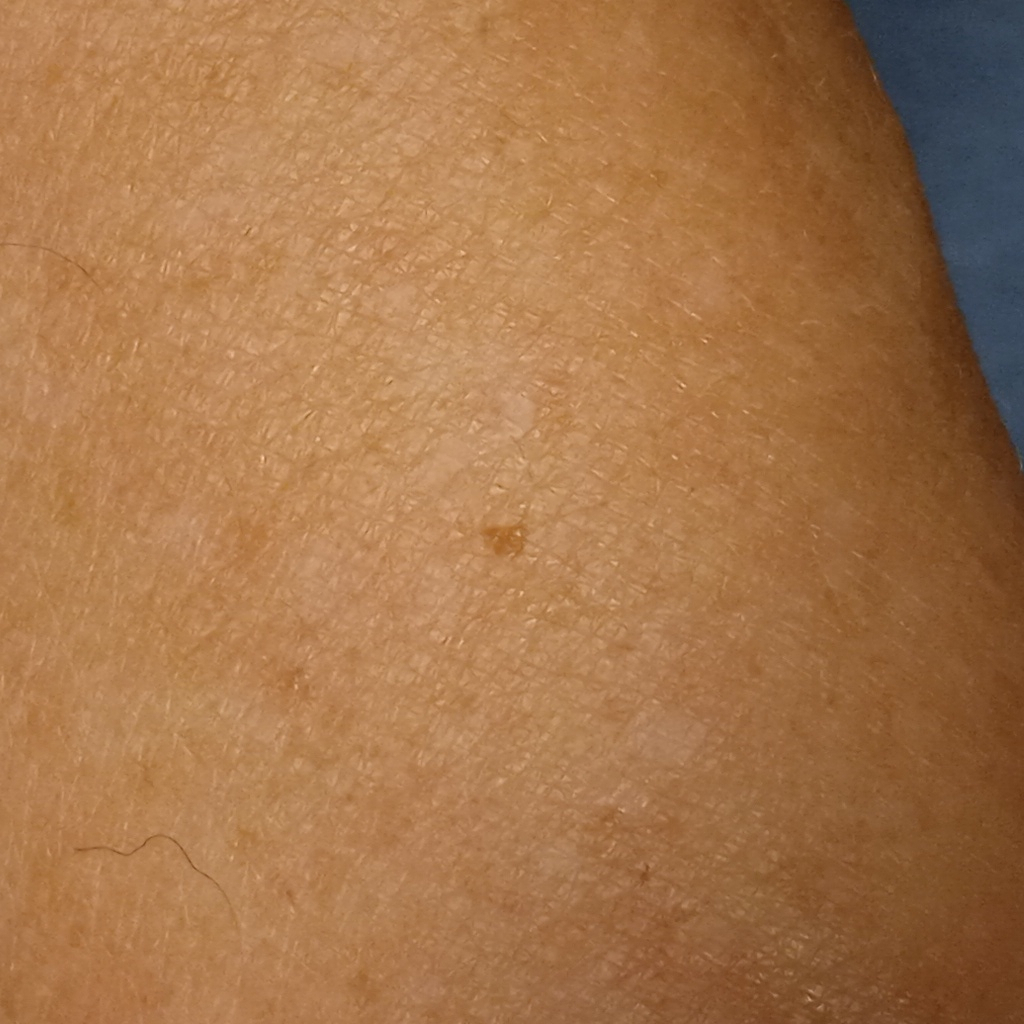A female subject 68 years old.
The patient says their skin tans without first burning.
Acquired for a research image collection, with no referral diagnosis.
Few moles overall by the patient's own estimate.
A clinical close-up of a skin lesion.
Located on an arm.
Dermatologist review favored a melanocytic nevus.